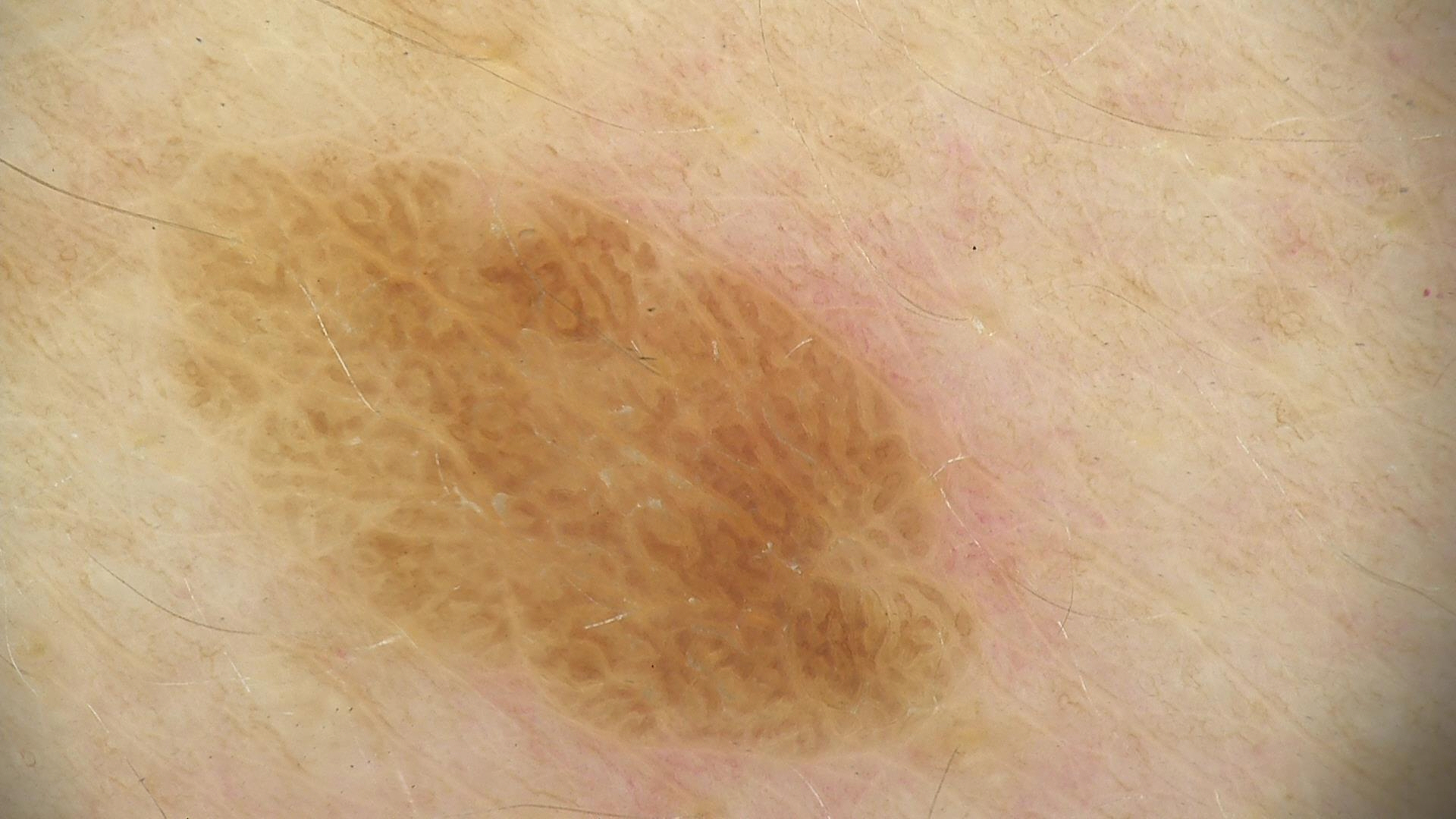{"diagnosis": {"name": "seborrheic keratosis", "code": "sk", "malignancy": "benign", "super_class": "non-melanocytic", "confirmation": "expert consensus"}}